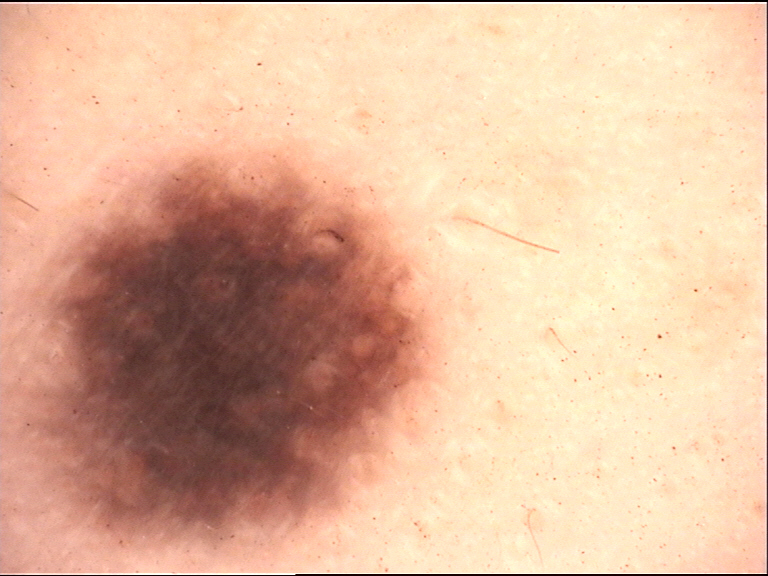Case:
* image type · dermoscopy
* class · compound nevus (expert consensus)